The contributor is female; the patient reported no systemic symptoms; the photograph is a close-up of the affected area; reported duration is about one day; symptoms reported: bothersome appearance and itching; located on the head or neck, back of the hand, palm, front of the torso, top or side of the foot, back of the torso and arm; the lesion is described as fluid-filled and raised or bumpy; the patient described the issue as a rash.
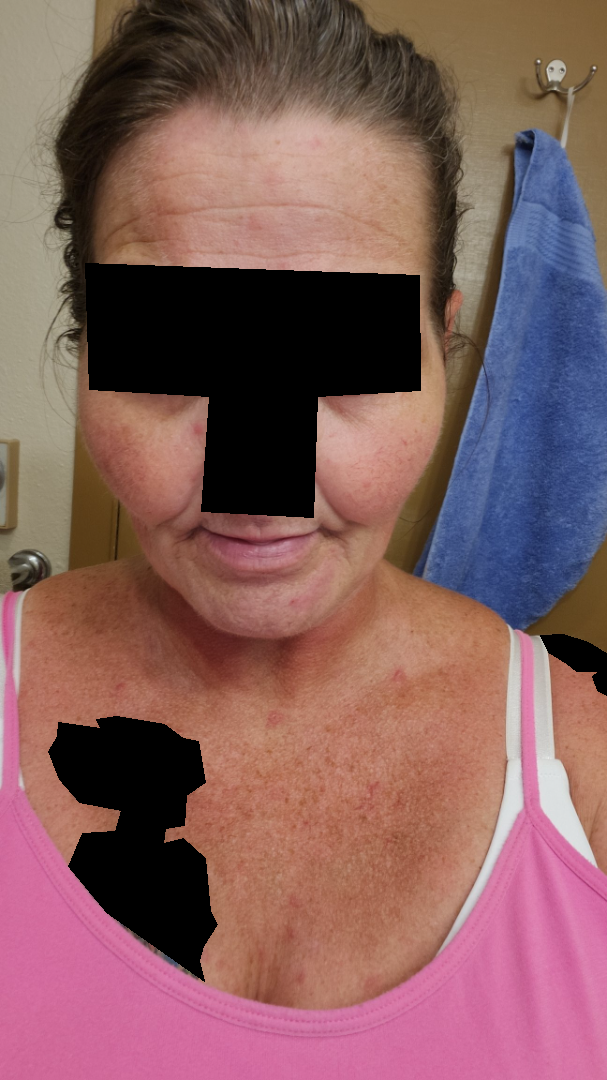assessment=ungradable on photographic review.